A dermoscopic image of a skin lesion.
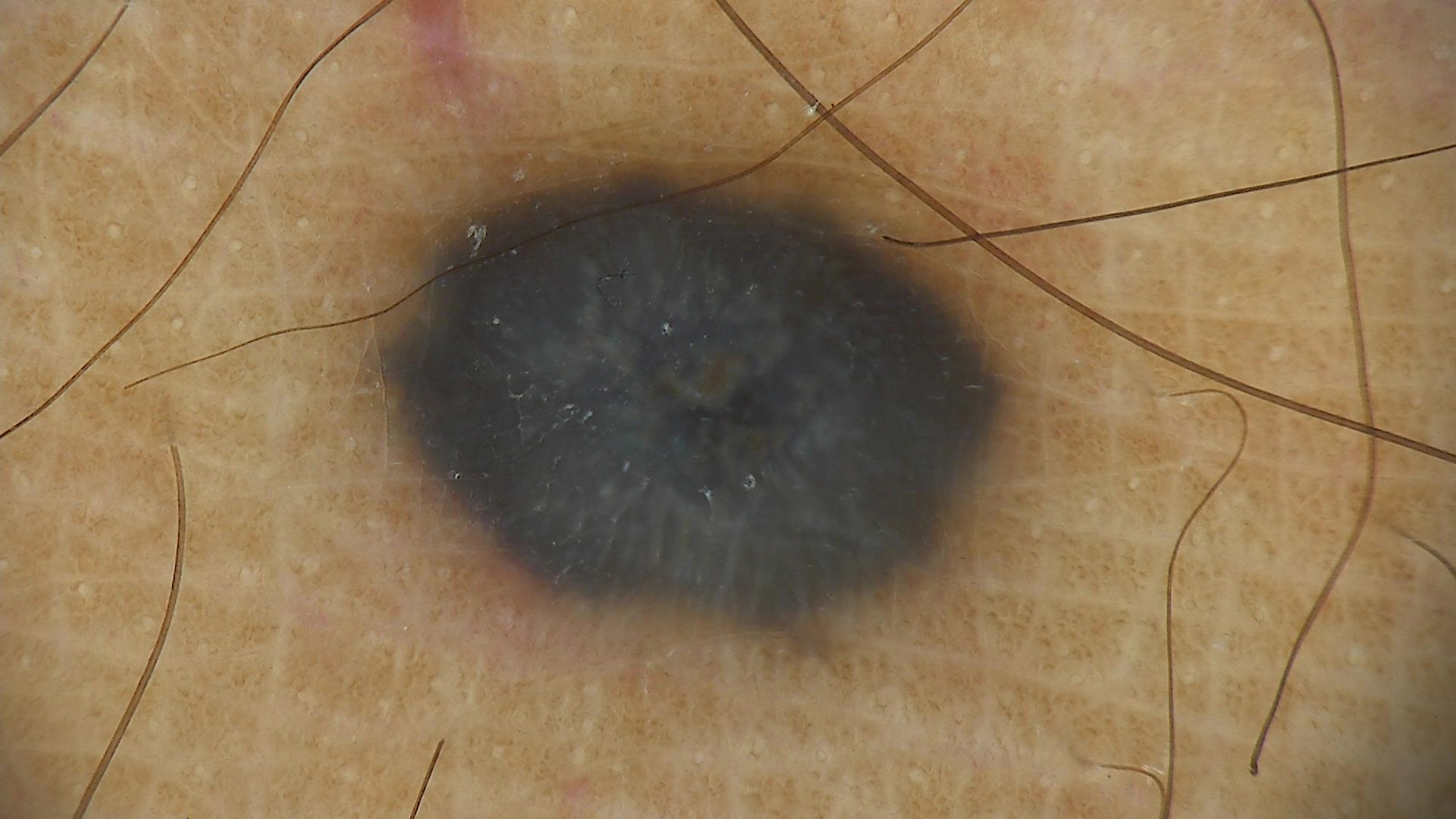The morphology is that of a dermal, banal lesion. The diagnosis was a blue nevus.